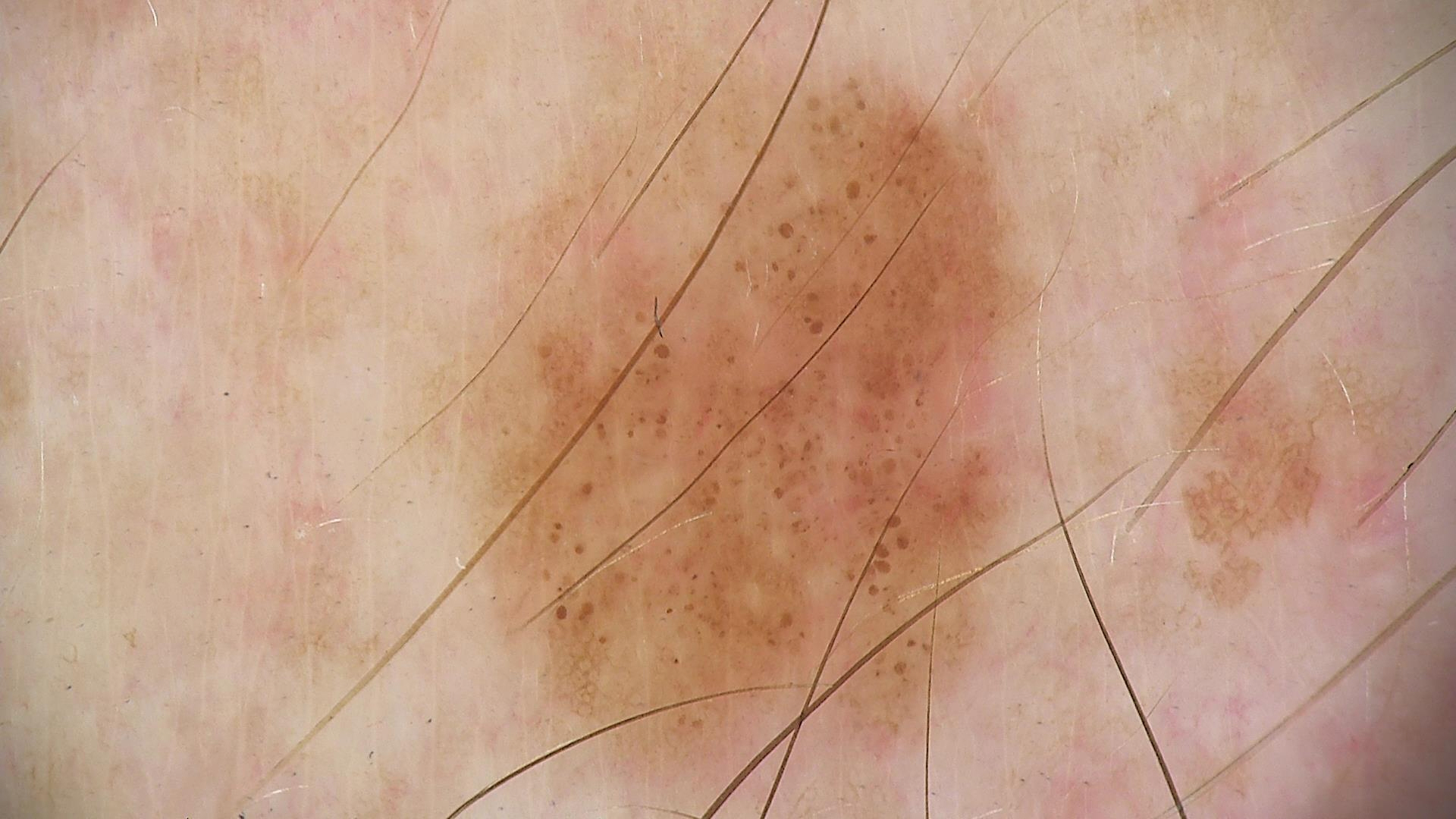Case: A skin lesion imaged with a dermatoscope. Conclusion: Classified as a dysplastic junctional nevus.